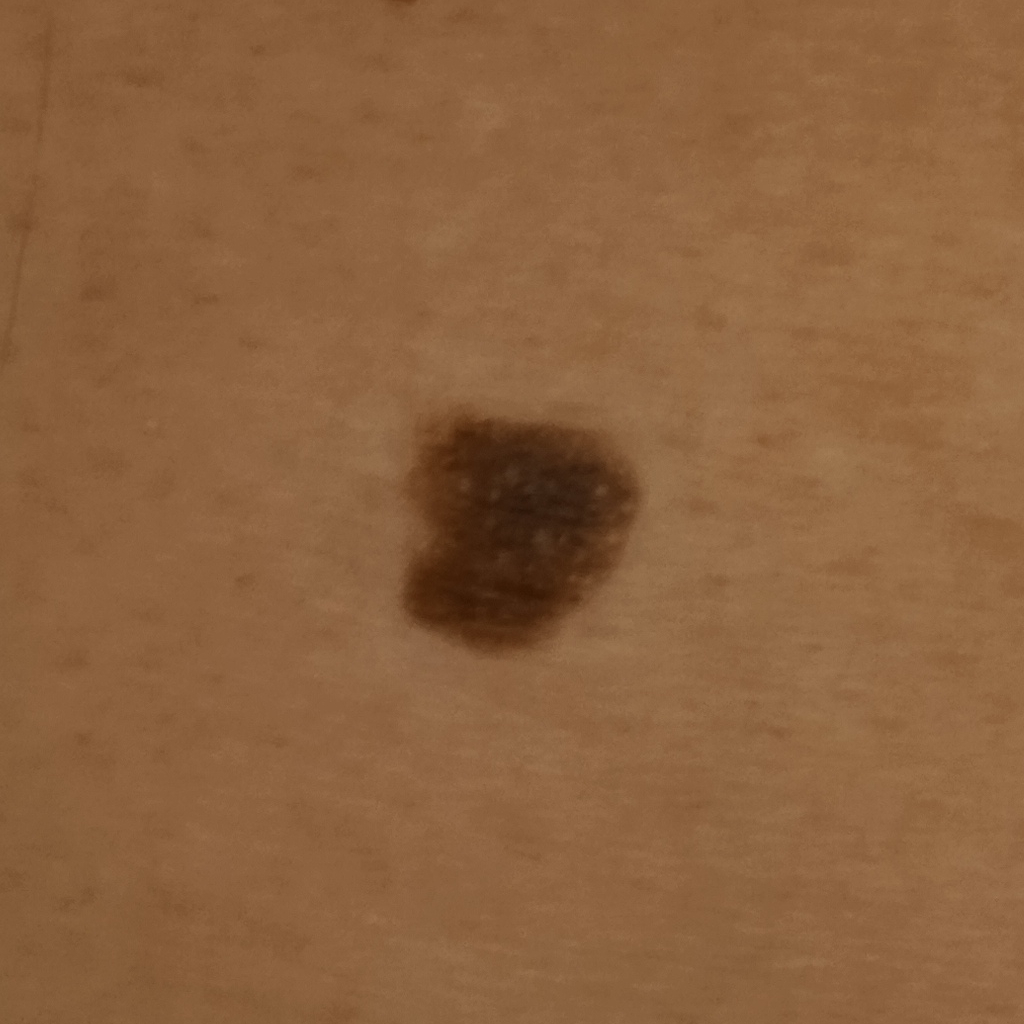Q: Tell me about the patient.
A: male, 76 years old
Q: Why was this imaged?
A: research study (no referral diagnosis)
Q: How does the patient's skin react to sun?
A: skin reddens with sun exposure
Q: What is the patient's nevus burden?
A: few melanocytic nevi overall
Q: What is the imaging modality?
A: clinical photograph
Q: What are the relevant risk factors?
A: a personal history of cancer, a personal history of skin cancer, no prior organ transplant
Q: Lesion size?
A: 8.6 mm
Q: What was the diagnosis?
A: seborrheic keratosis (dermatologist consensus)